Close-up view; located on the top or side of the foot — 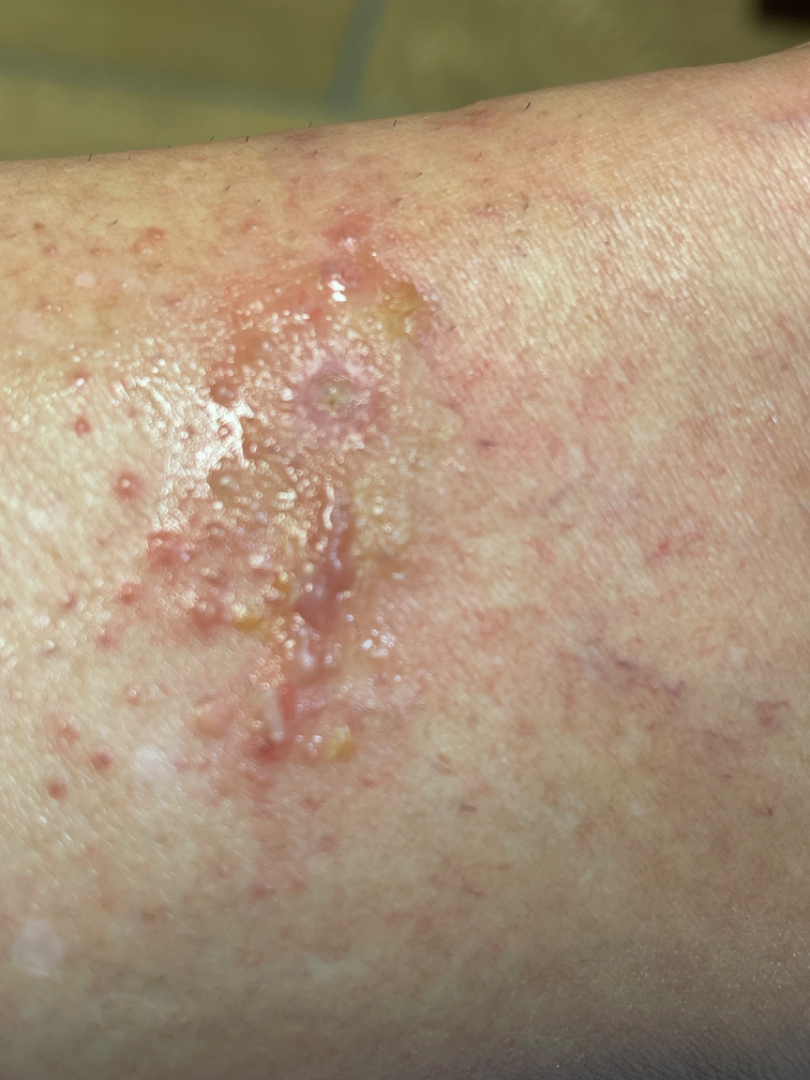skin tone: Fitzpatrick III; lay graders estimated Monk Skin Tone 3 | reported symptoms: bothersome appearance, burning, enlargement and itching | duration: one to four weeks | self-categorized as: a rash | assessment: most consistent with Allergic Contact Dermatitis; an alternative is Impetigo; lower on the differential is Infected eczema.